A clinical photograph of a skin lesion · the patient was assessed as Fitzpatrick phototype IV.
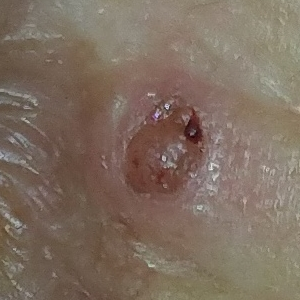The lesion is located on the nose. The patient describes that the lesion itches, is elevated, has bled, and has grown. Histopathological examination showed a basal cell carcinoma.